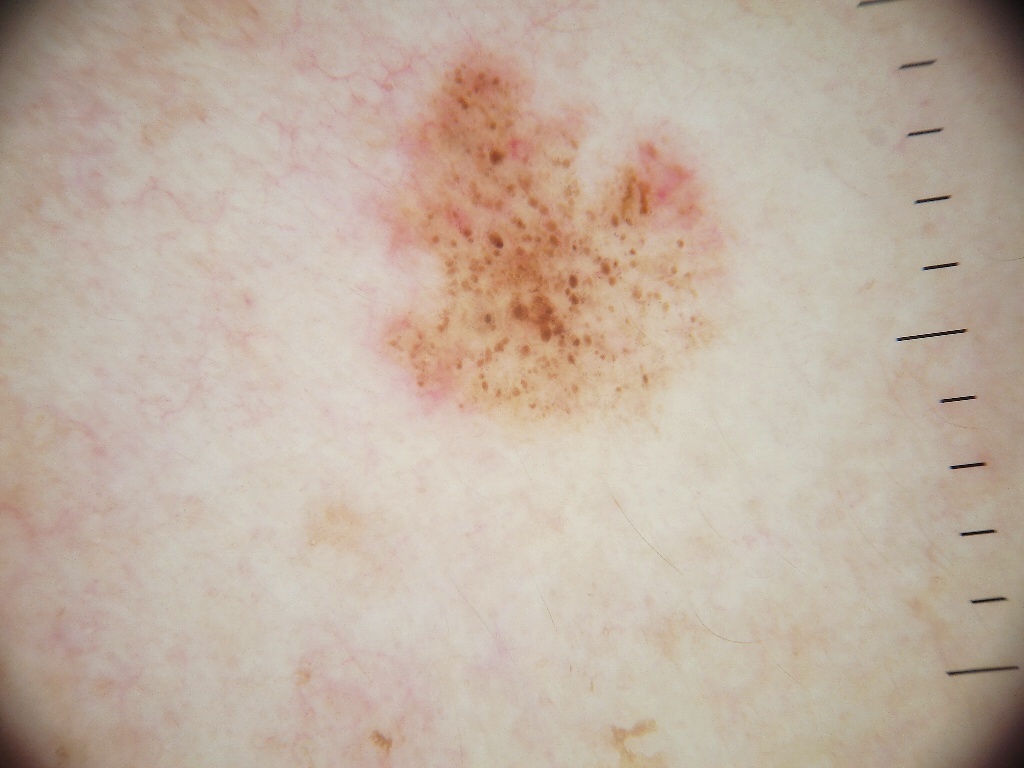image type: dermatoscopic image of a skin lesion; location: <box>351, 29, 746, 452</box>; lesion extent: ~17% of the field; impression: a skin cancer.